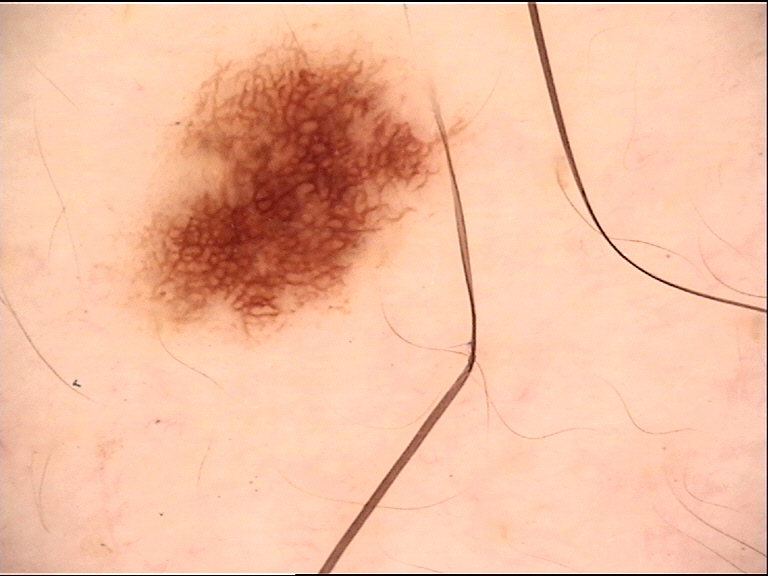label: junctional nevus (expert consensus)